No constitutional symptoms were reported, this is a close-up image, the contributor reports the lesion is fluid-filled and raised or bumpy, the patient described the issue as skin that appeared healthy to them, the affected area is the head or neck — 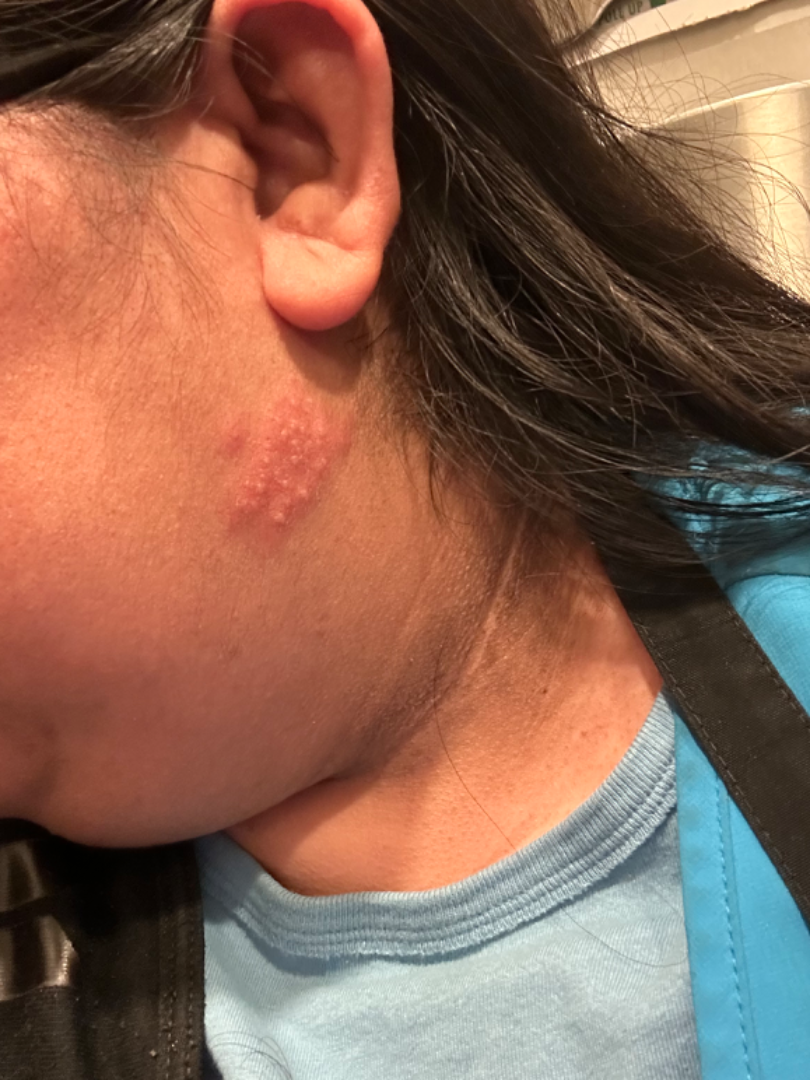Consistent with Herpes Simplex.